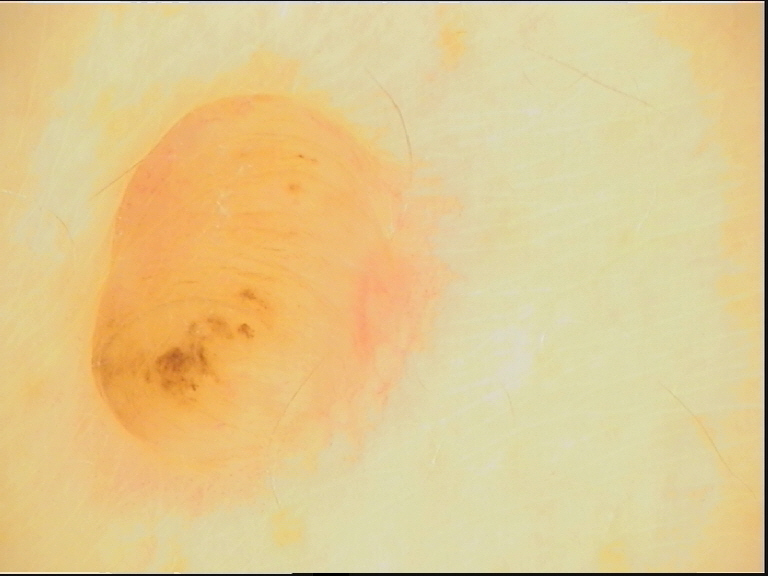<dermoscopy>
<image>dermatoscopy</image>
<lesion_type>
<main_class>banal</main_class>
<pattern>dermal</pattern>
</lesion_type>
<diagnosis>
<name>dermal nevus</name>
<code>db</code>
<malignancy>benign</malignancy>
<super_class>melanocytic</super_class>
<confirmation>expert consensus</confirmation>
</diagnosis>
</dermoscopy>